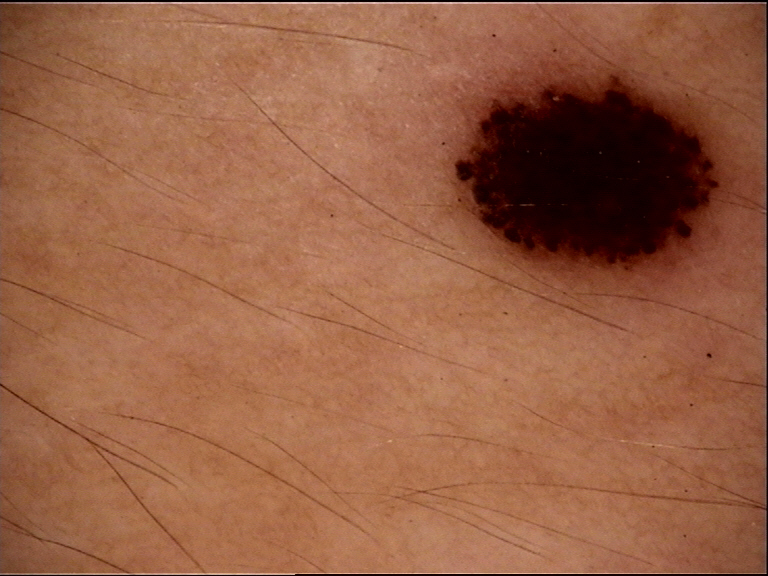A dermoscopic close-up of a skin lesion.
Consistent with a benign lesion — a Spitz/Reed nevus.